The patient is a male about 45 years old; a dermatoscopic image of a skin lesion:
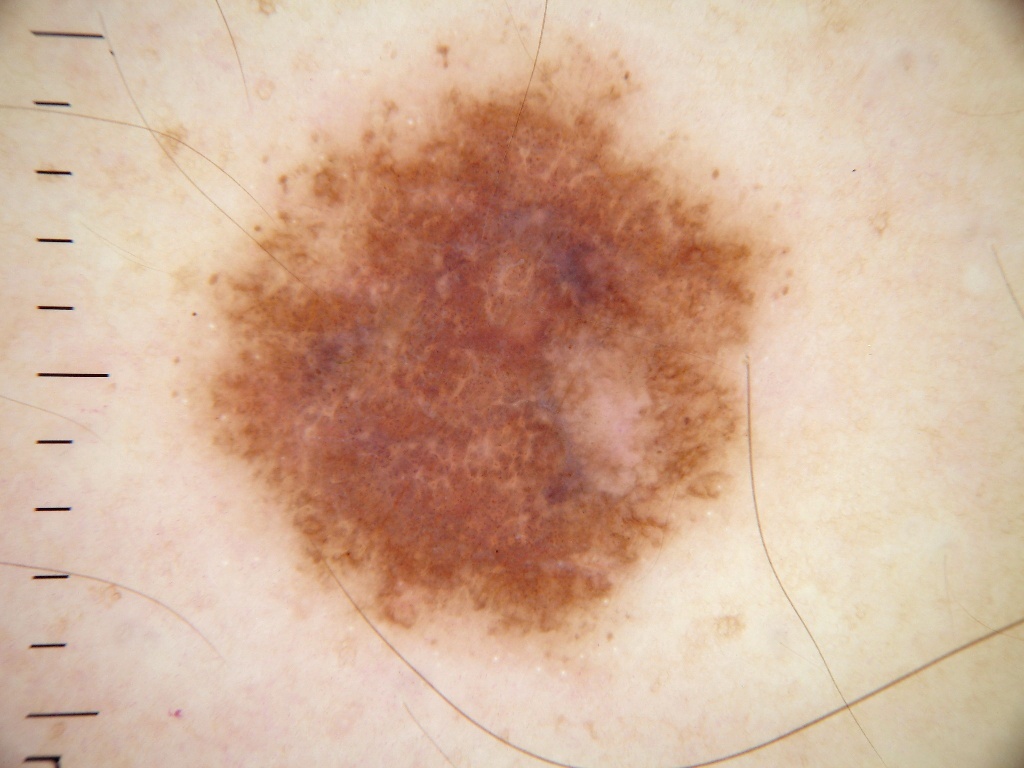dermoscopic pattern: globules, milia-like cysts, and negative network
lesion size: large
location: [152,4,803,681]
assessment: a melanocytic nevus, a benign skin lesion